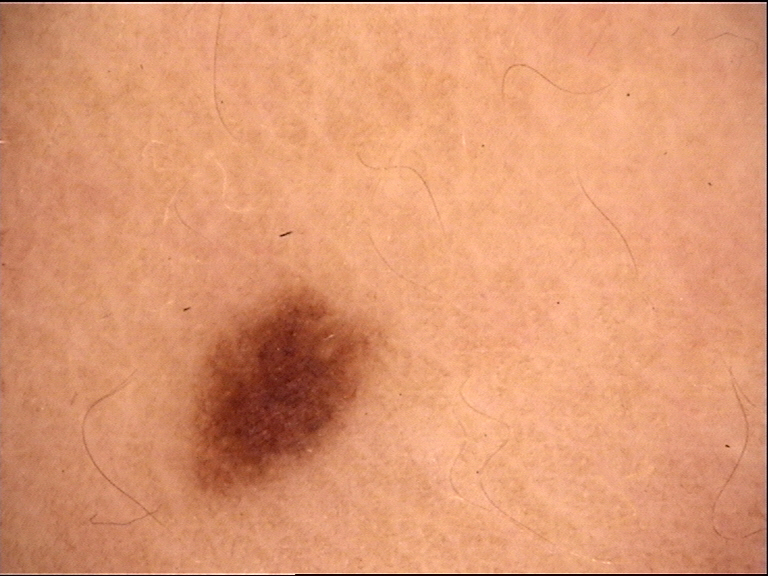A dermatoscopic image of a skin lesion.
The diagnosis was a junctional nevus.